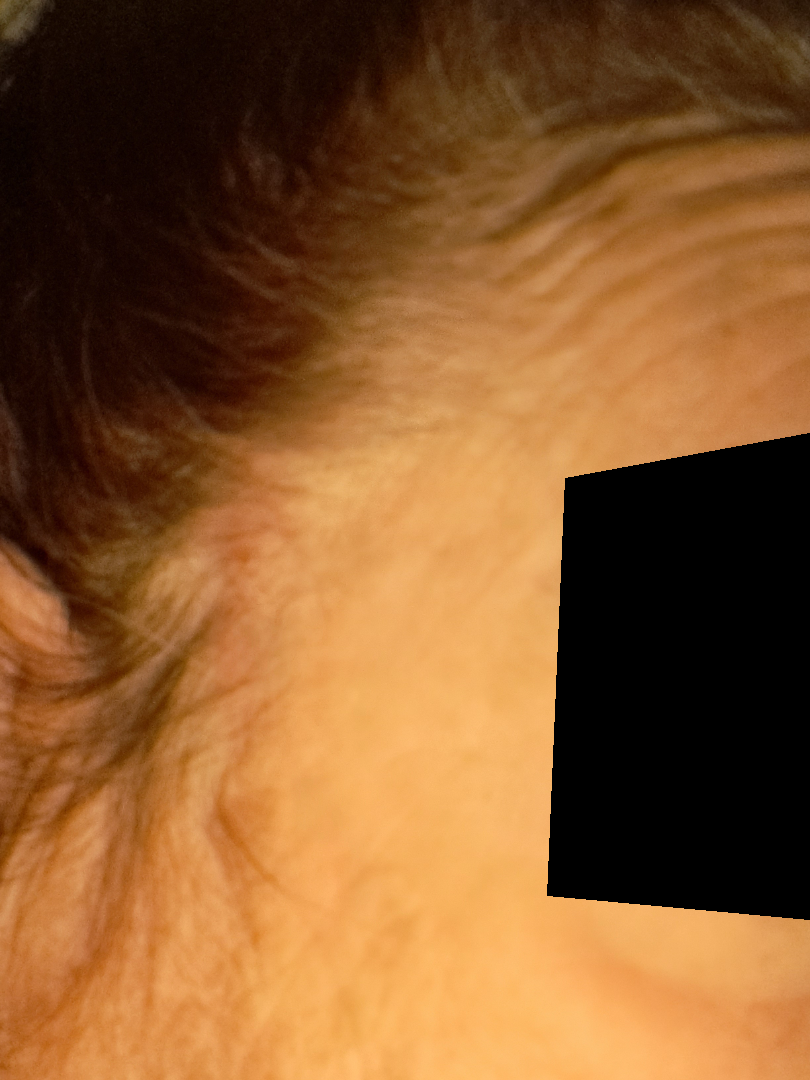assessment = indeterminate from the photograph | patient describes the issue as = skin that appeared healthy to them | photo taken = at an angle | body site = head or neck | subject = female | duration = more than one year | lesion texture = raised or bumpy | other reported symptoms = fatigue | lesion symptoms = enlargement, itching and bothersome appearance.